Present for three to twelve months · the affected area is the back of the torso · the patient notes associated fatigue and joint pain · the patient reported no relevant symptoms from the lesion · female subject, age 40–49 · the patient described the issue as skin that appeared healthy to them · texture is reported as flat · the photograph is a close-up of the affected area.
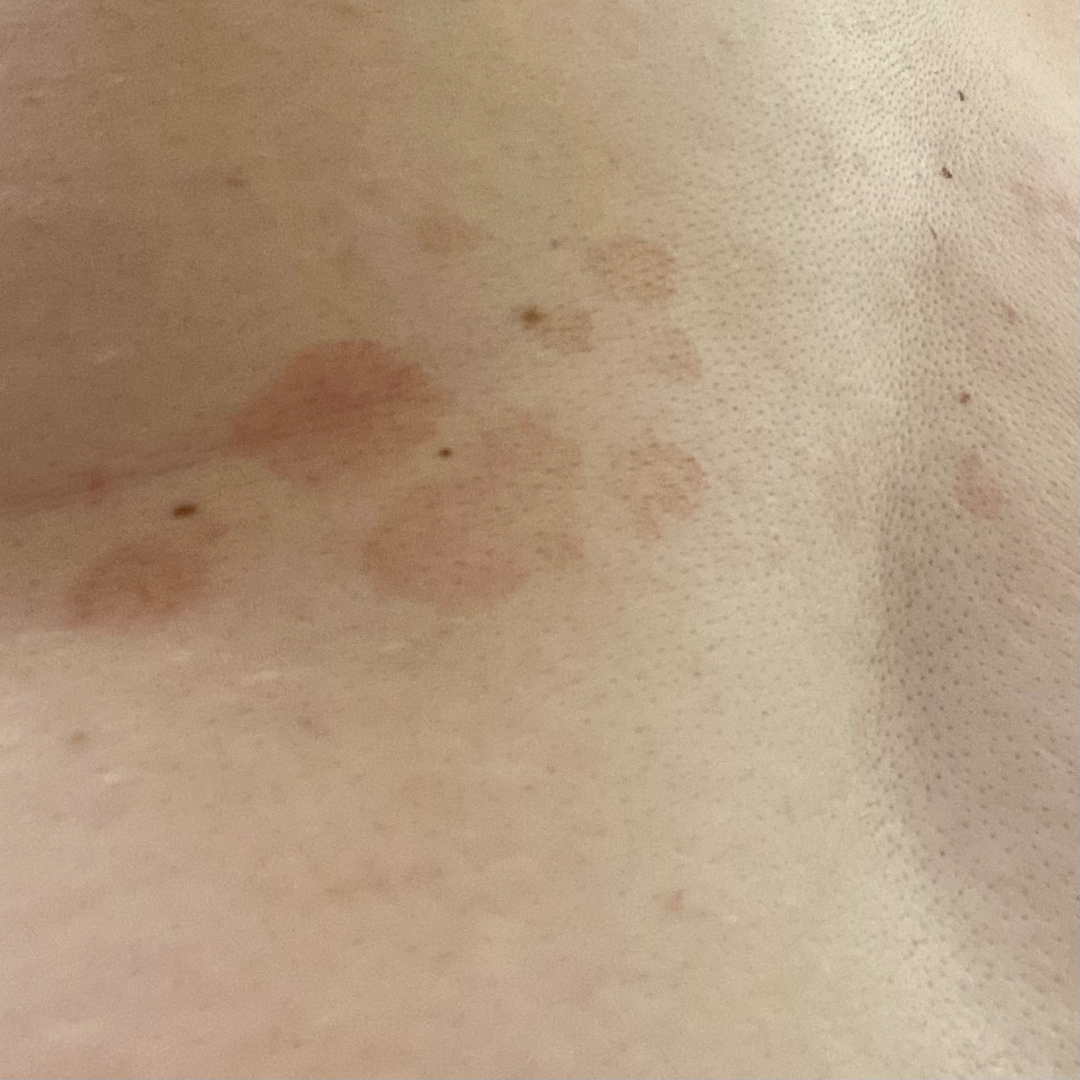dermatologist impression = reviewed remotely by one dermatologist: the favored diagnosis is Tinea Versicolor; also consider Seborrheic Dermatitis.